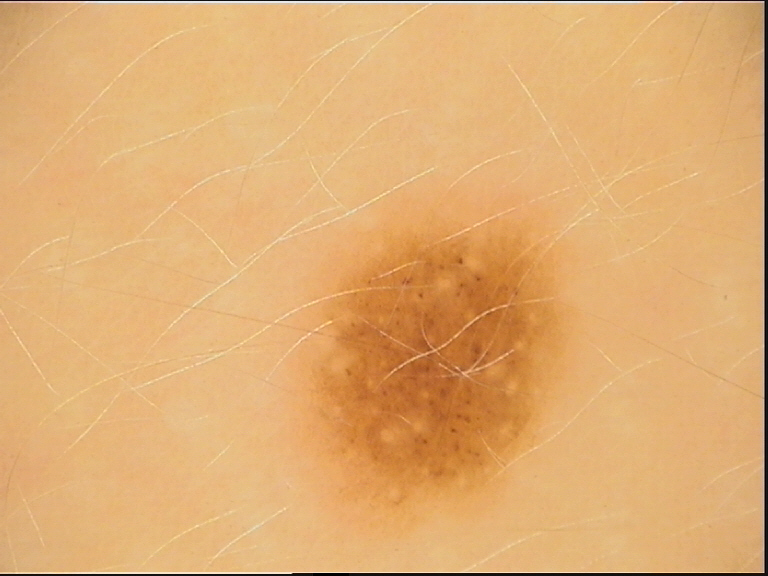Consistent with a dysplastic junctional nevus.